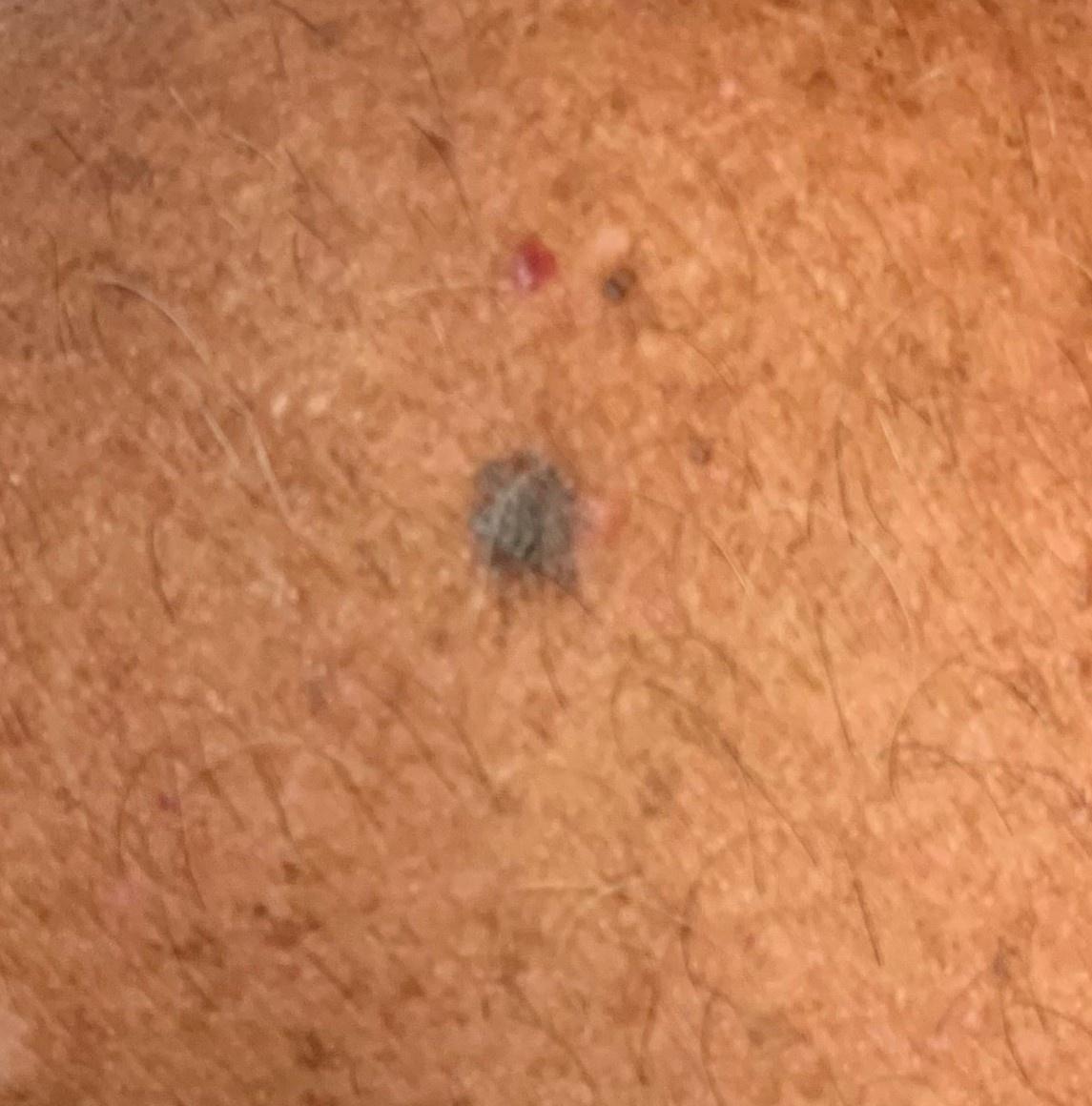Clinical context:
A clinical photograph of a skin lesion. A male subject in their mid-70s. The lesion was found on an upper extremity.
Pathology:
On biopsy, the diagnosis was a melanoma.